Dermoscopy of a skin lesion.
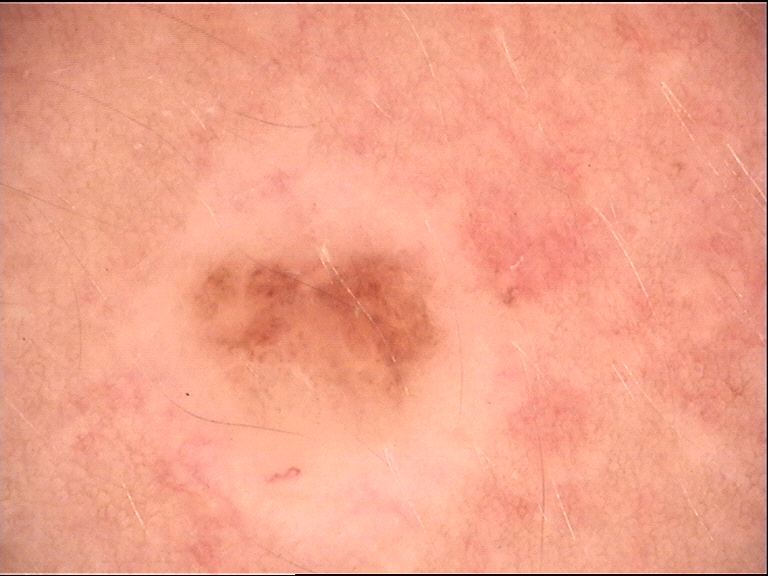The diagnostic label was a banal lesion — a compound nevus.